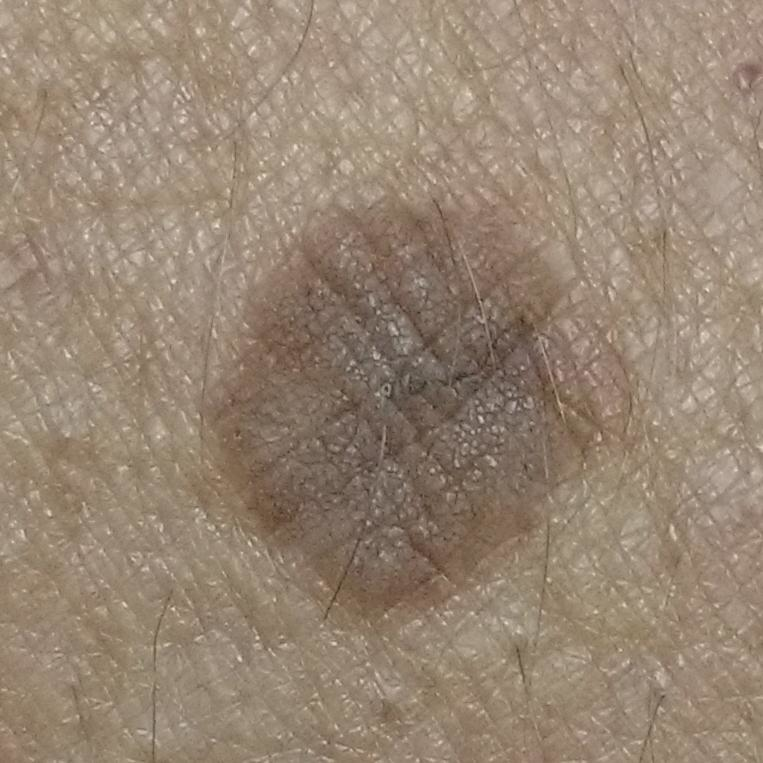By the patient's account, the lesion has grown, has changed, and is elevated, but has not bled.
Diagnosed by dermatologist consensus as a seborrheic keratosis.